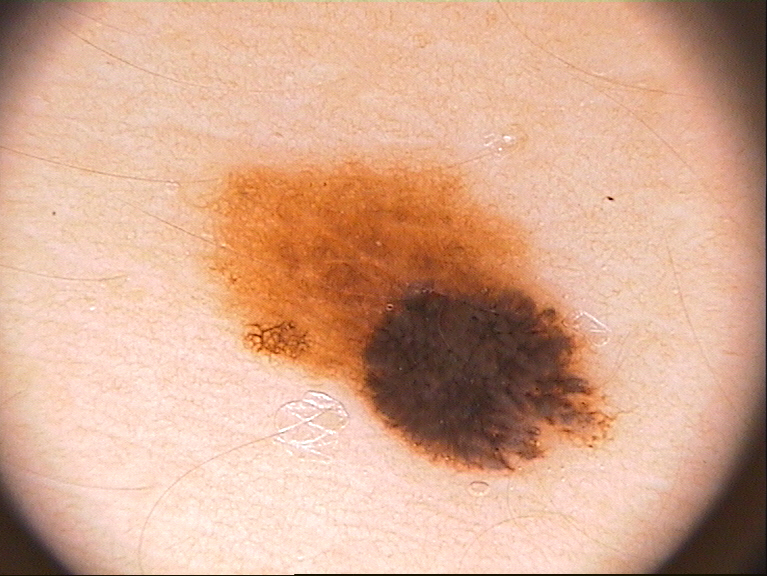Q: What kind of image is this?
A: dermoscopic image
Q: Where is the lesion located?
A: (188, 148, 630, 480)
Q: Which dermoscopic features were noted?
A: streaks and pigment network
Q: How large is the lesion within the image?
A: moderate
Q: What did the assessment conclude?
A: a melanocytic nevus